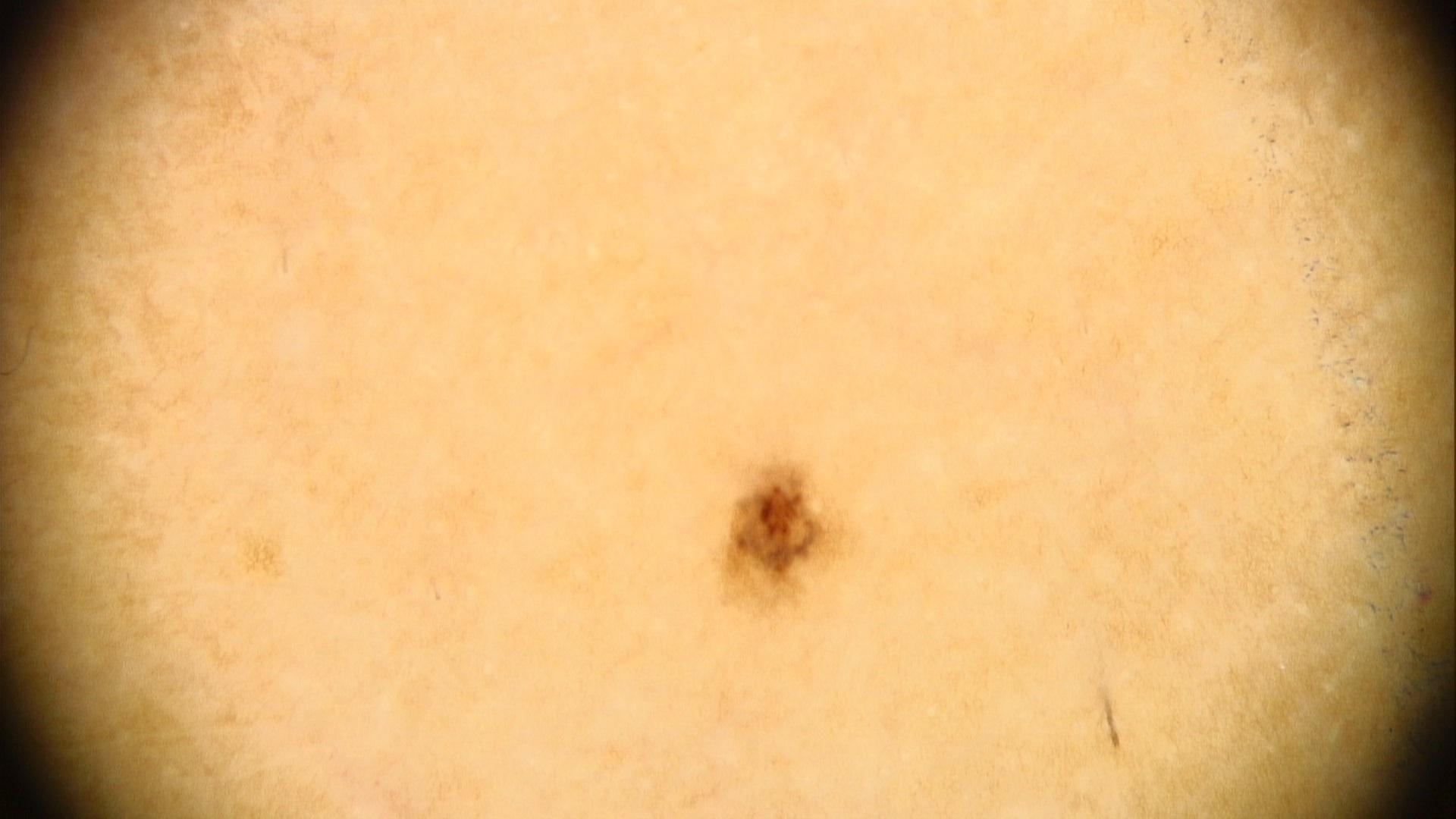Case:
• assessment: Nevus